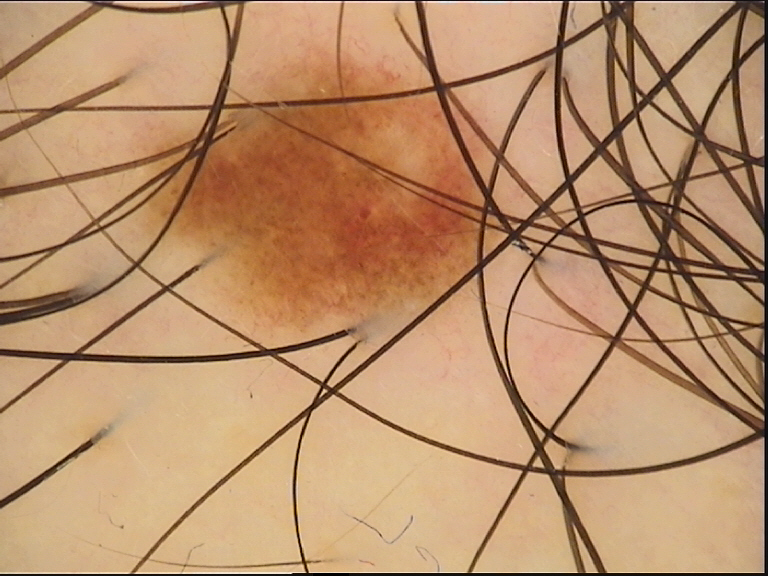- diagnosis · dysplastic junctional nevus (expert consensus)